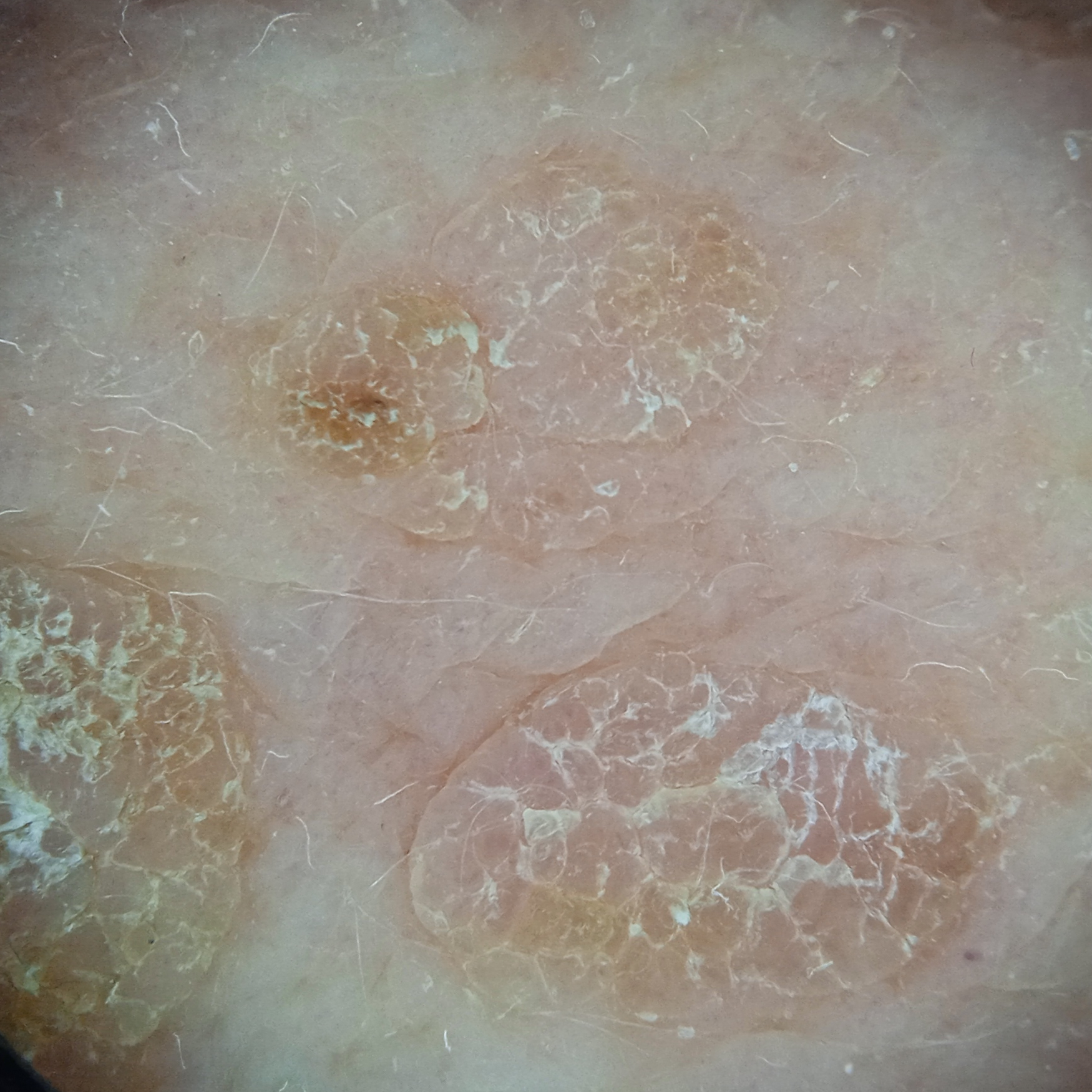A dermoscopic image of a skin lesion.
The lesion involves the back.
The lesion measures approximately 10.6 mm.
Four dermatologists reviewed the lesion; the consensus was a seborrheic keratosis; the four reviewers were unanimous; the reviewers were fairly confident.